A dermatoscopic image of a skin lesion.
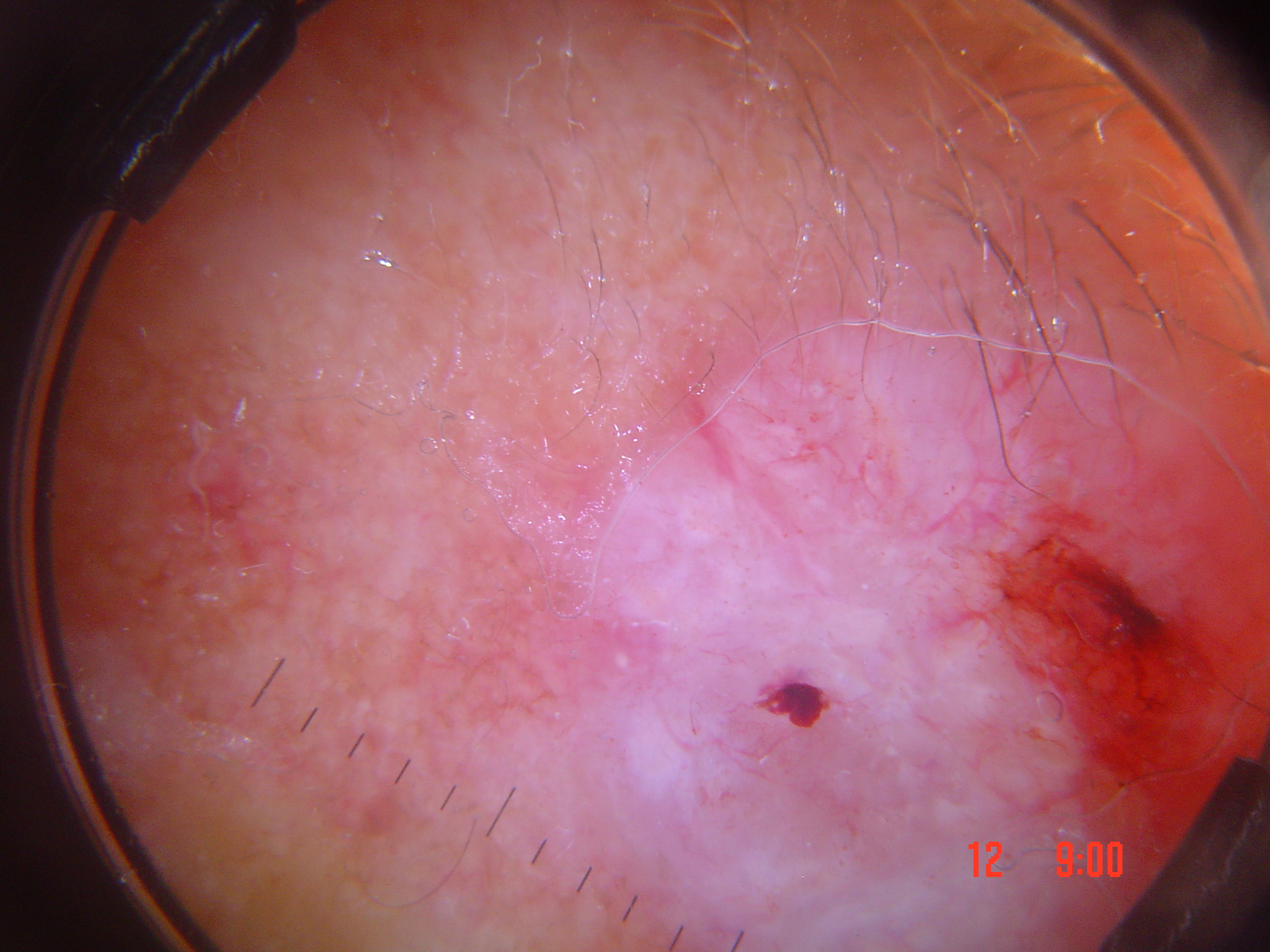Conclusion:
Biopsy-confirmed as a keratinocytic lesion — a basal cell carcinoma.